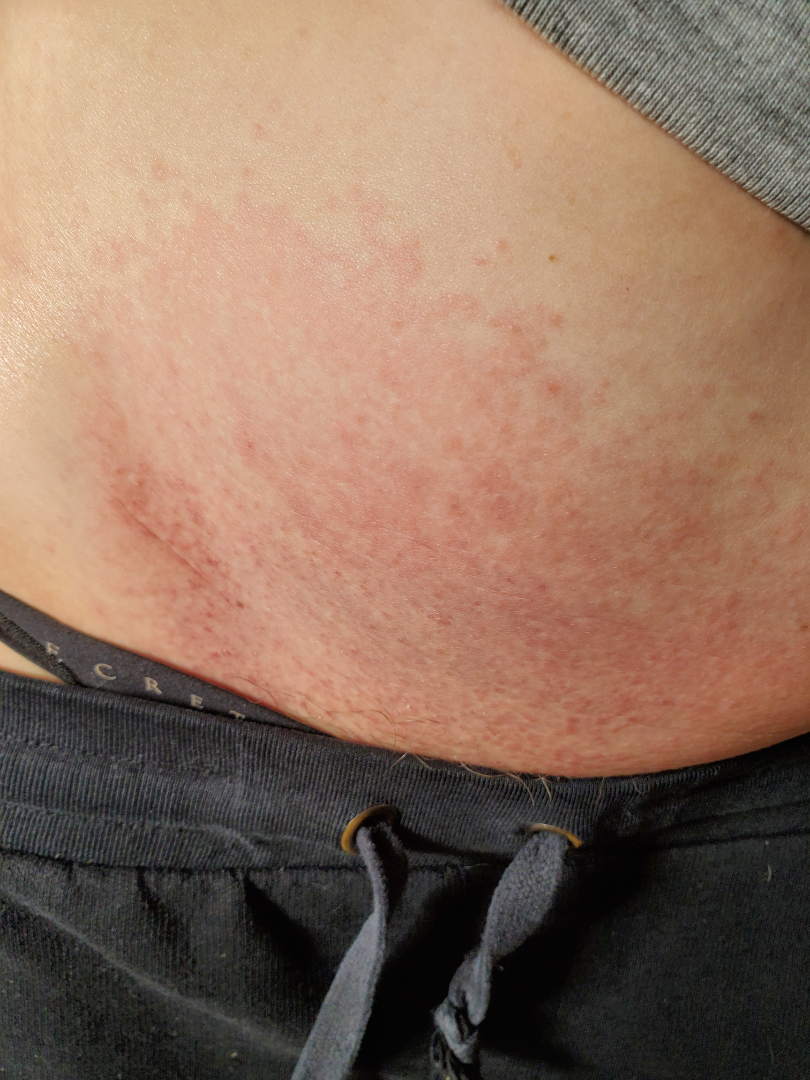Q: Duration?
A: more than five years
Q: Reported symptoms?
A: enlargement, bothersome appearance, itching, burning and pain
Q: What is the lesion texture?
A: raised or bumpy and rough or flaky
Q: Any systemic symptoms?
A: fatigue, chills and joint pain
Q: Patient's own categorization?
A: a rash
Q: What is the framing?
A: at an angle
Q: What conditions are considered?
A: Eczema (leading)